A dermoscopic photograph of a skin lesion:
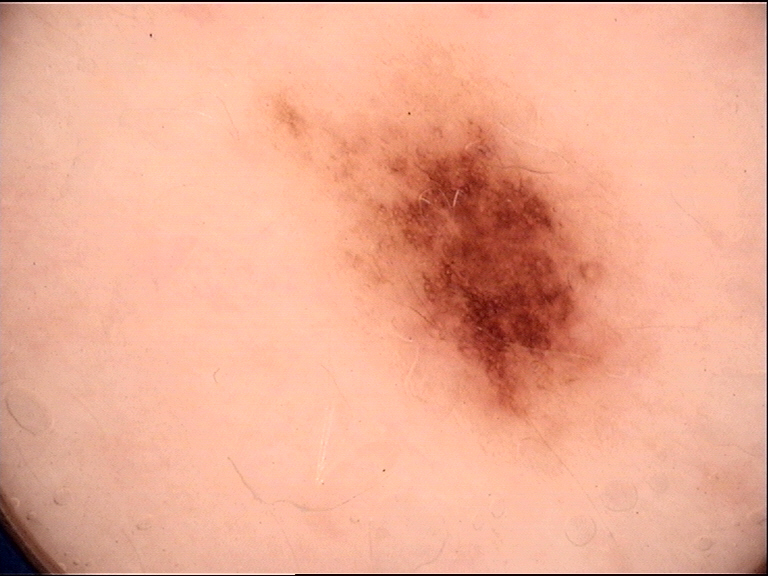Q: What is this lesion?
A: dysplastic junctional nevus (expert consensus)